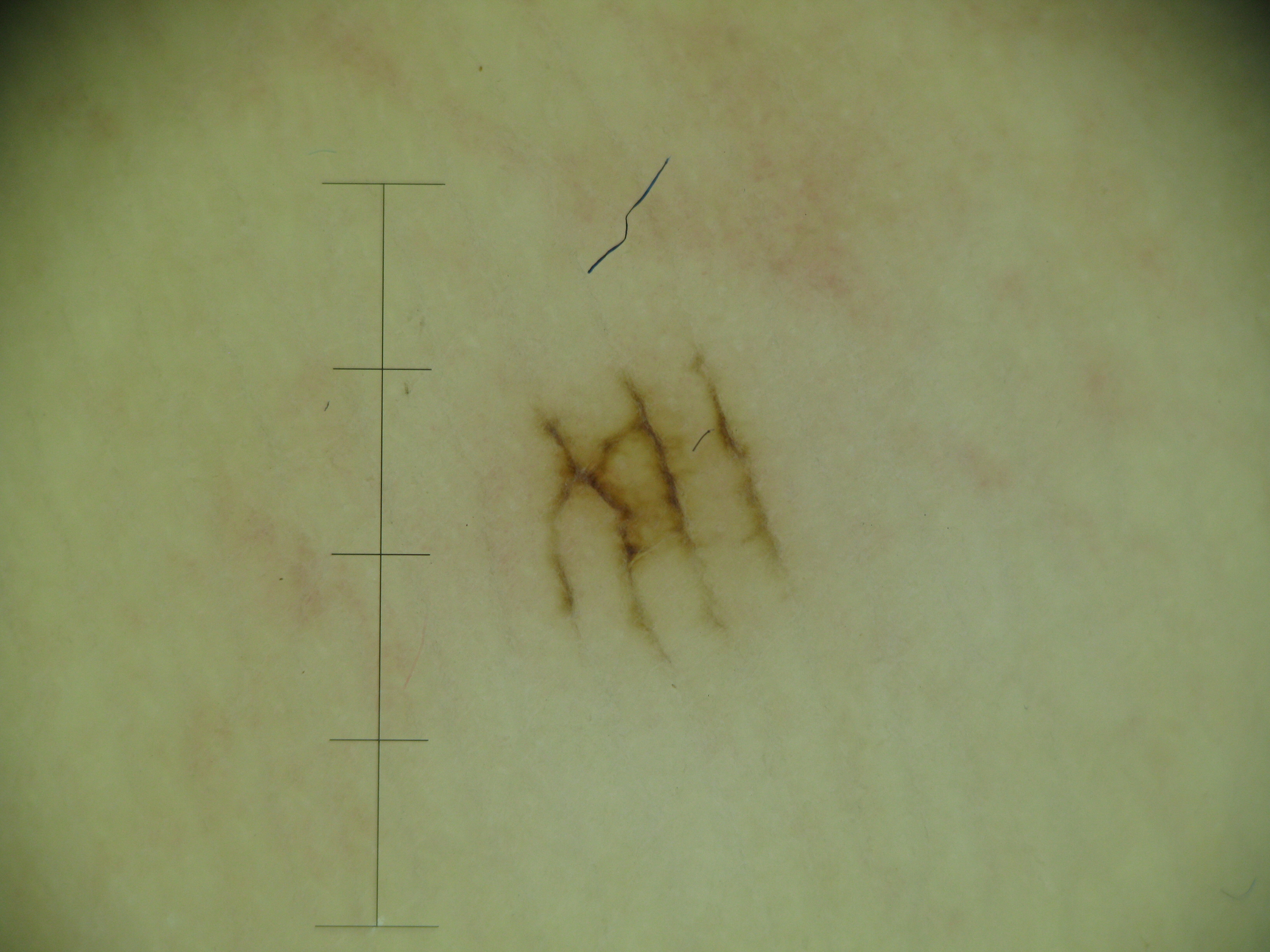A skin lesion imaged with a dermatoscope.
Labeled as a banal lesion — an acral junctional nevus.